The photo was captured at an angle:
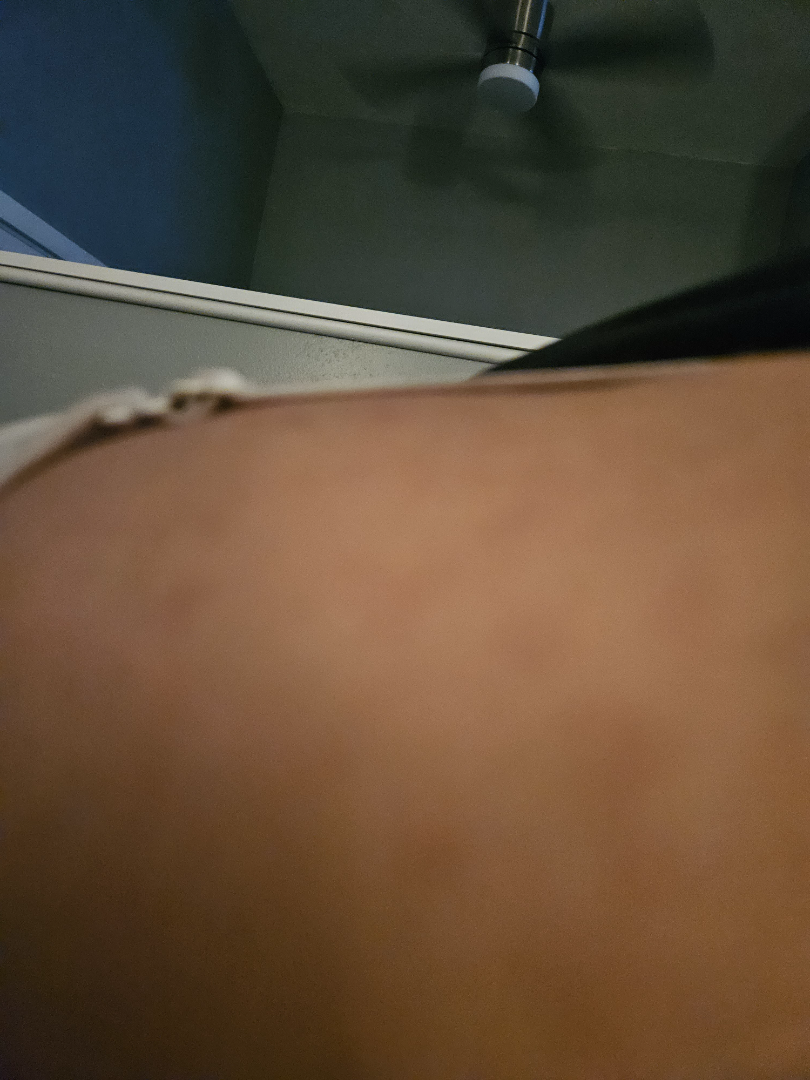Reviewed remotely by one dermatologist: the favored diagnosis is Tinea Versicolor; an alternative is Post-Inflammatory hyperpigmentation.